A clinical close-up photograph of a skin lesion. A subject in their 50s — 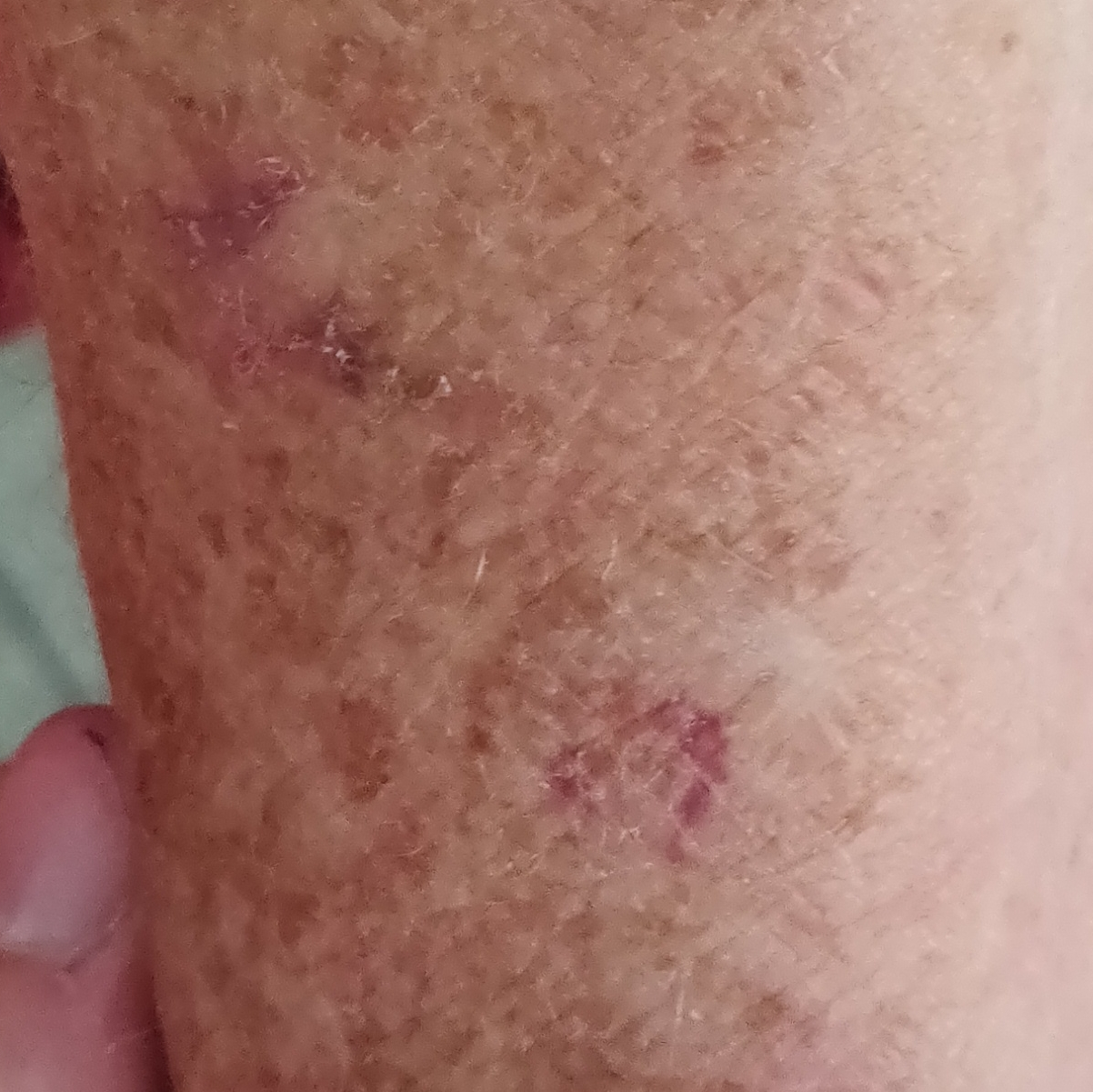site: a forearm
patient-reported symptoms: elevation, growth, itching
impression: actinic keratosis (clinical consensus)